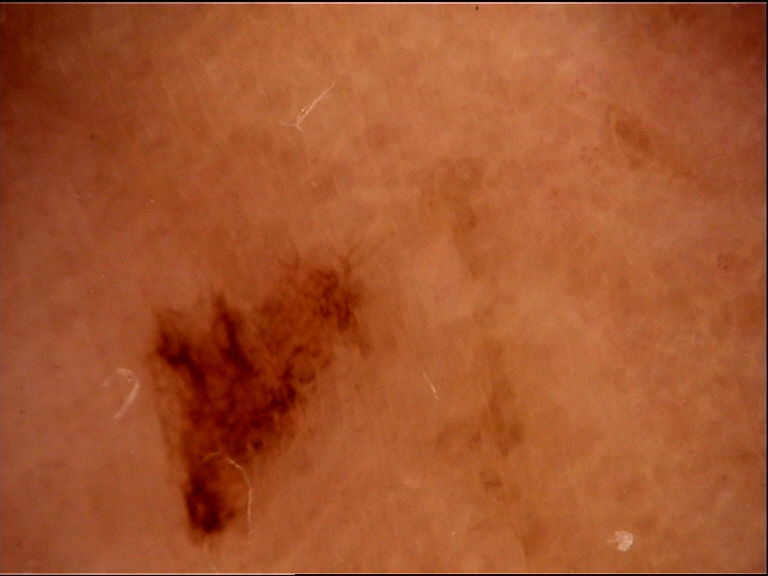Impression: The diagnosis was a benign lesion — an acral dysplastic junctional nevus.